The patient described the issue as a rash · this image was taken at an angle · located on the palm and arm — 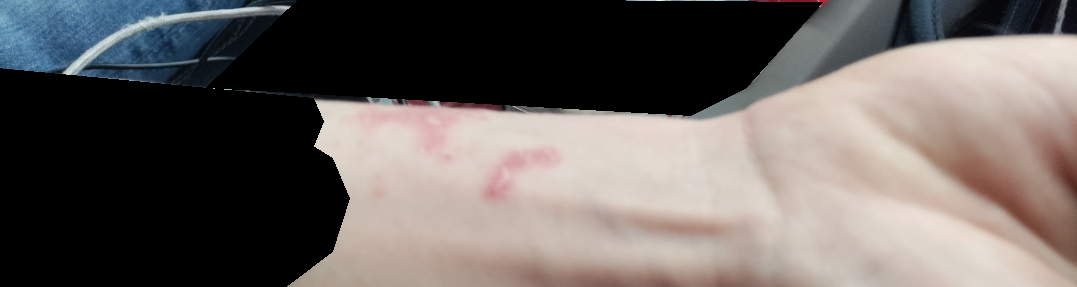diagnostic considerations: the leading impression is Psoriasis; also raised was Eczema; the differential also includes Lichen planus/lichenoid eruption